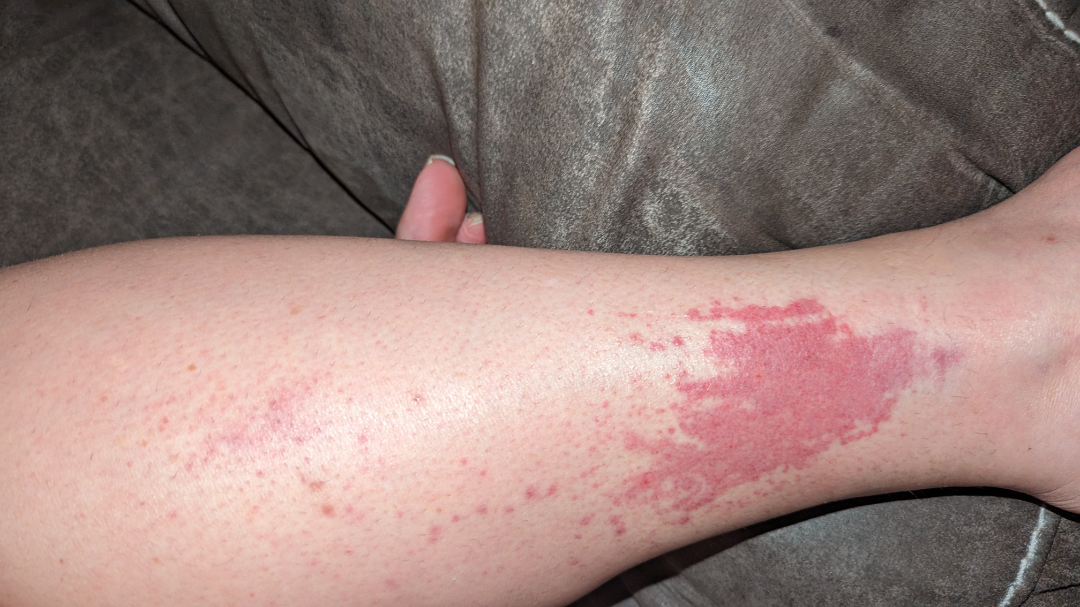body_site: leg
shot_type: close-up
patient_category: a rash
duration: less than one week
systemic_symptoms: none reported
symptoms:
  - burning
  - itching
  - bothersome appearance
differential:
  tied_lead:
    - Allergic Contact Dermatitis
    - Leukocytoclastic Vasculitis
  unlikely:
    - Abrasion, scrape, or scab